This is a dermoscopic photograph of a skin lesion: 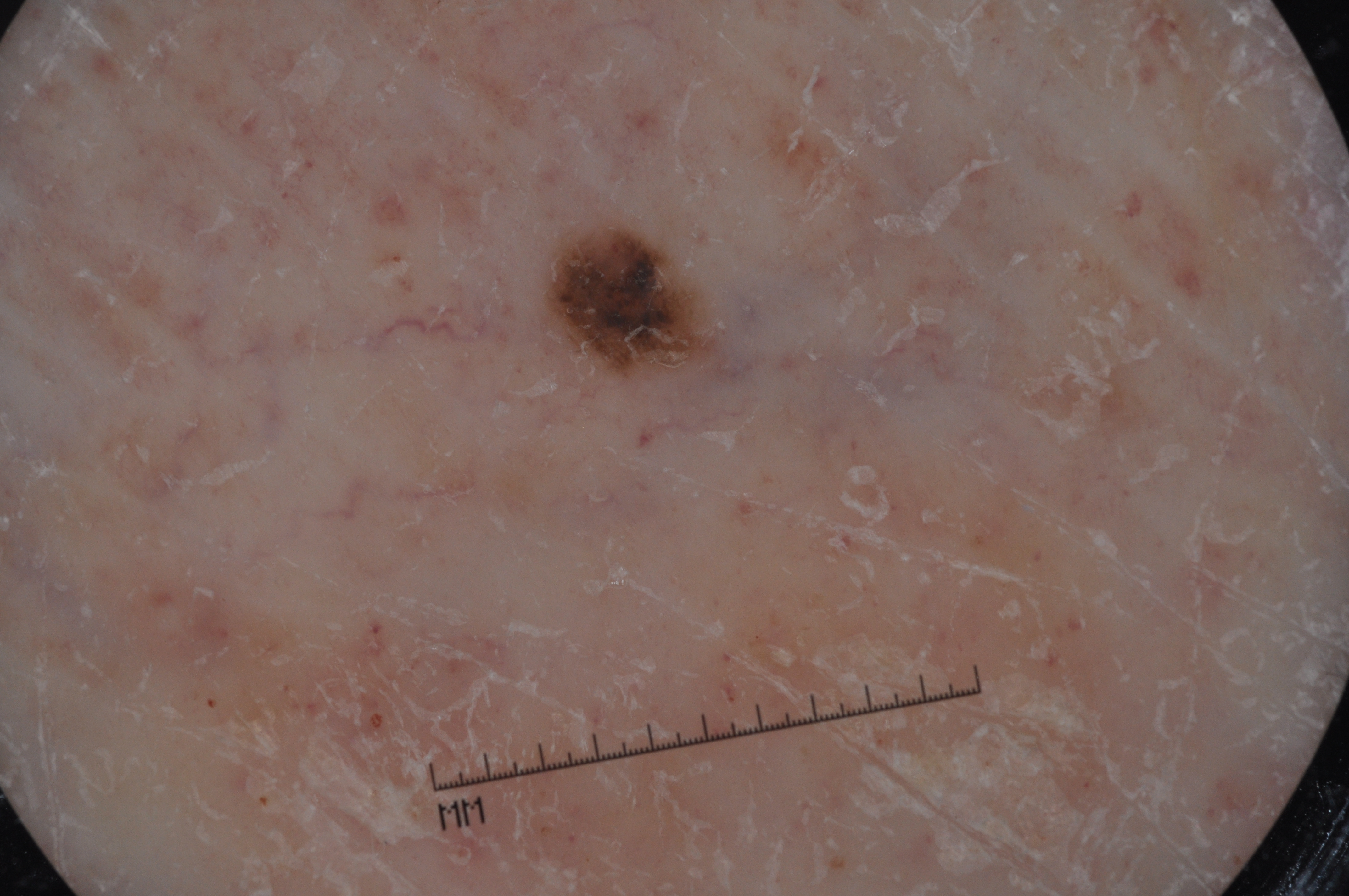Dermoscopic examination shows pigment network; no negative network, milia-like cysts, or streaks. The visible lesion spans <bbox>548, 231, 706, 371</bbox>. Consistent with a melanocytic nevus, a benign lesion.